Located on the leg; the photograph was taken at a distance — 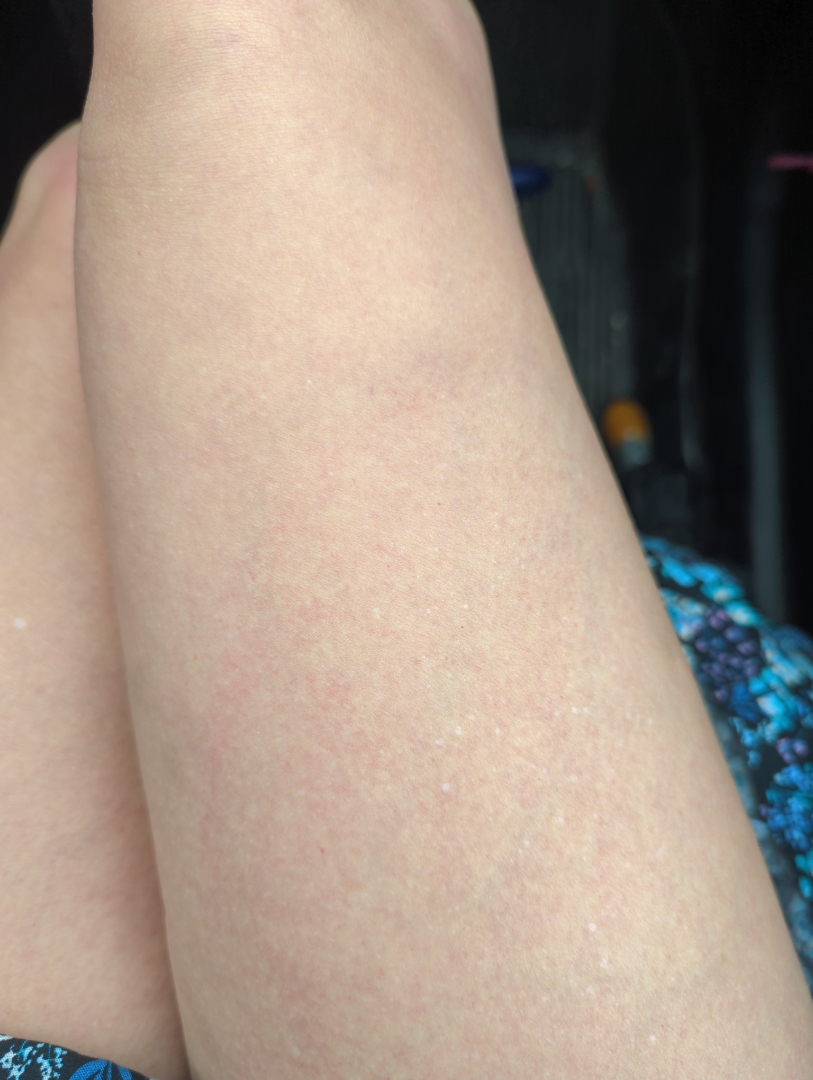The reviewer was unable to grade this case for skin condition. Skin tone: Fitzpatrick skin type III; non-clinician graders estimated 1 on the Monk Skin Tone. No associated systemic symptoms reported. Self-categorized by the patient as a rash. Symptoms reported: bothersome appearance and itching. The patient reports the condition has been present for less than one week. Texture is reported as rough or flaky.